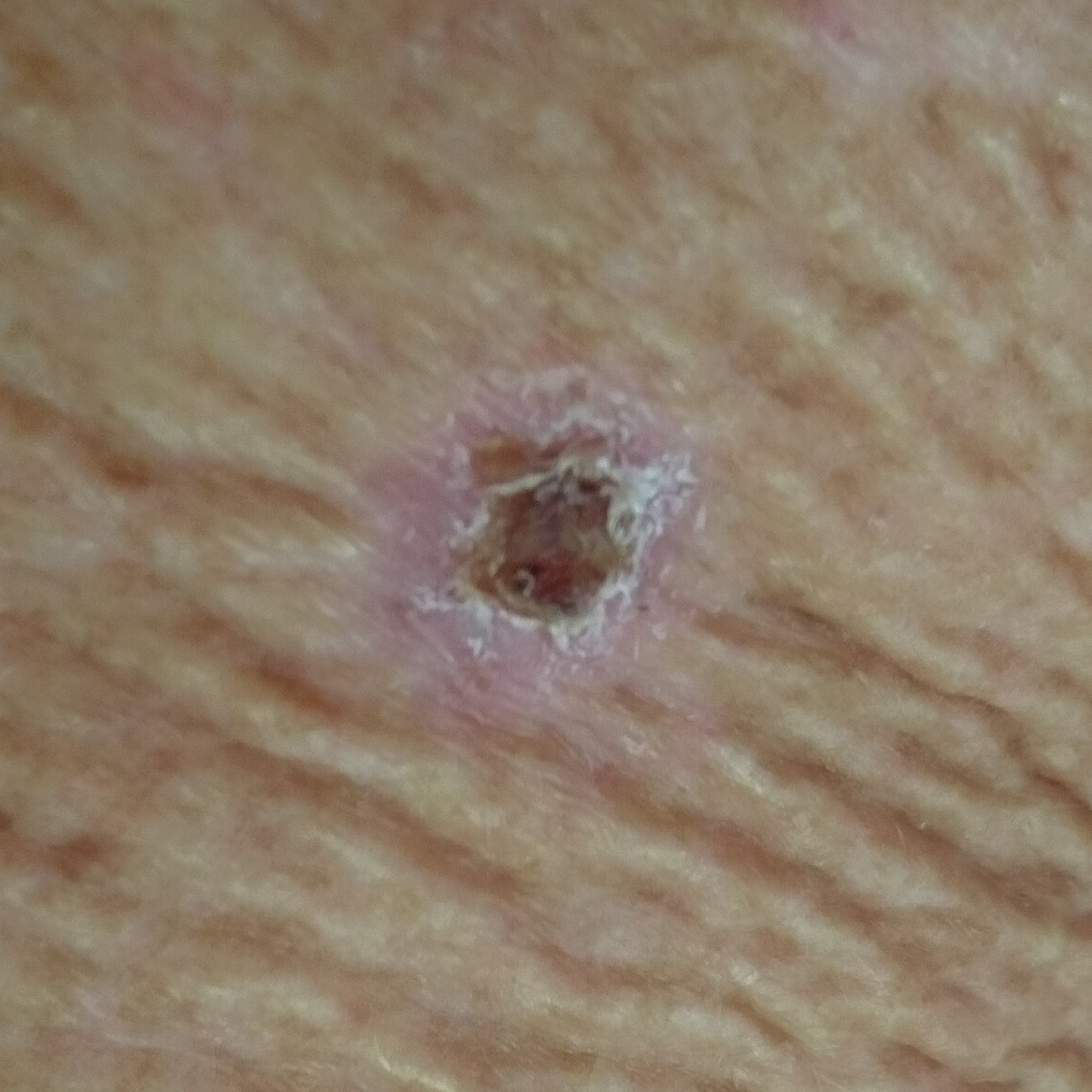imaging — smartphone clinical photo; diameter — approx. 11 × 10 mm; diagnostic label — basal cell carcinoma (biopsy-proven).